An image taken at an angle · the front of the torso and leg are involved · skin tone: FST I; lay reviewers estimated Monk Skin Tone 2–3 · self-categorized by the patient as a rash · texture is reported as flat · the contributor is 40–49, female · no relevant systemic symptoms · the contributor notes itching · the condition has been present for less than one week:
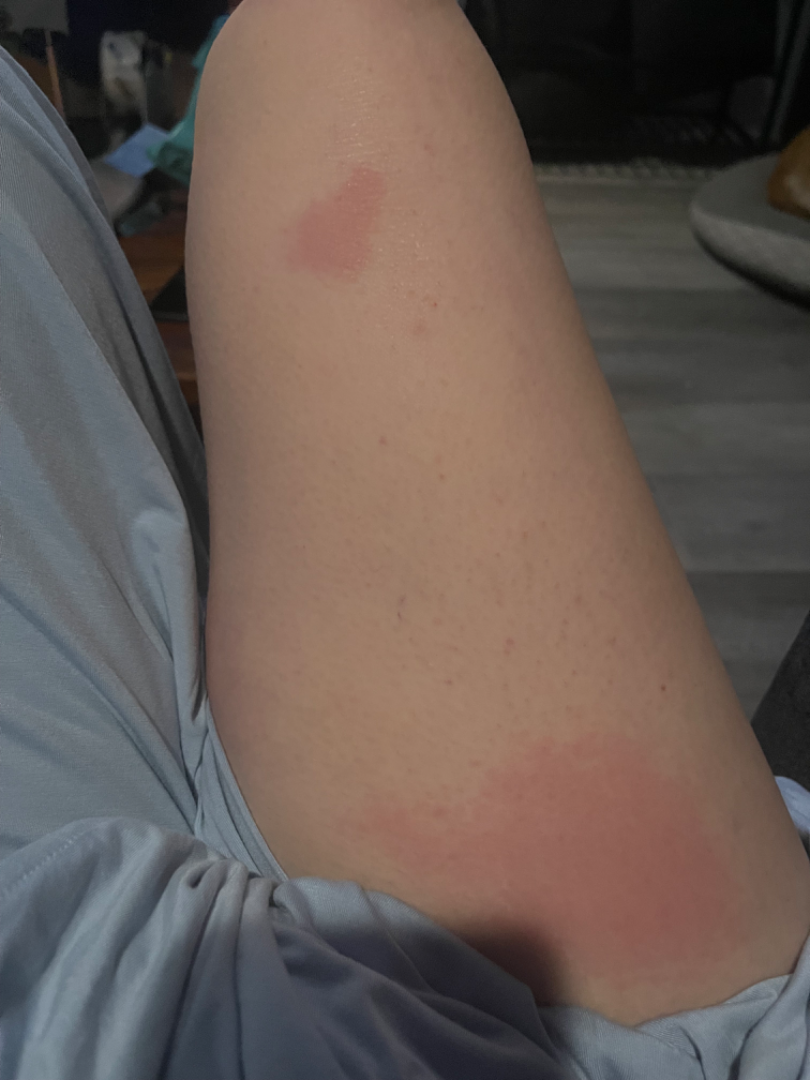Findings:
Contact dermatitis (favored); Acute dermatitis, NOS (less likely); Irritant Contact Dermatitis (less likely); Urticaria (less likely); Allergic Contact Dermatitis (less likely); Hypersensitivity (less likely).